The patient is a male aged 18–29, this is a close-up image, the affected area is the leg: 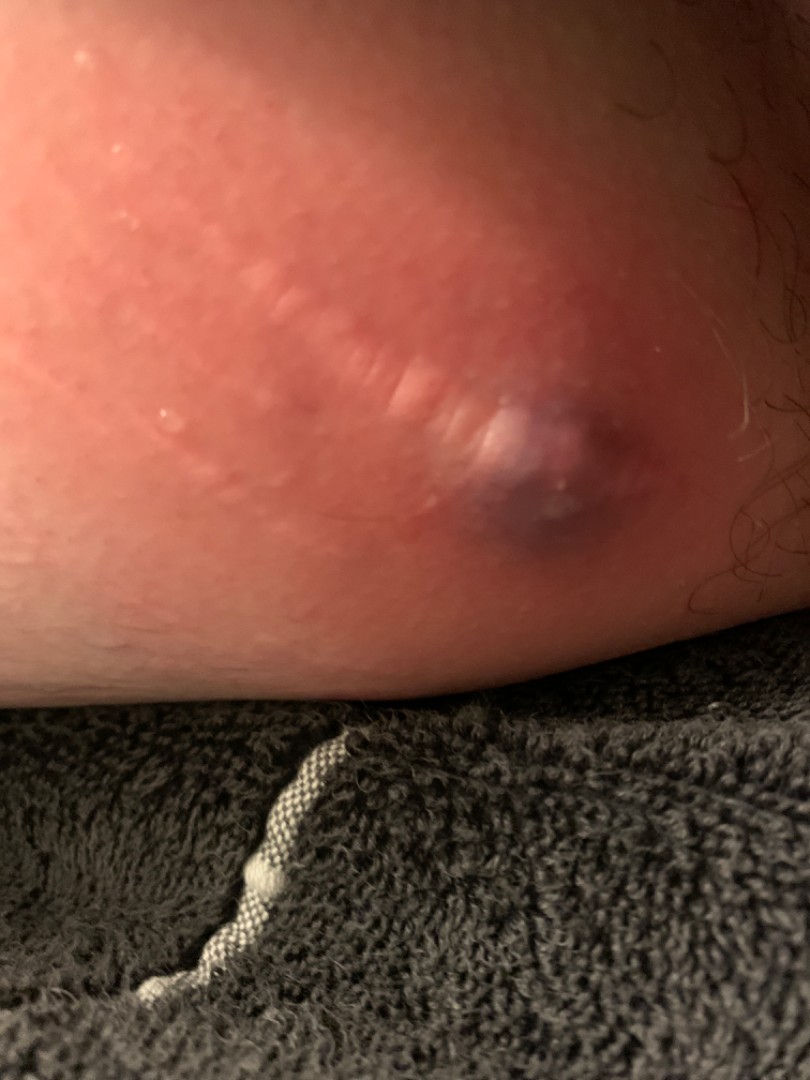Patient information: The condition has been present for less than one week. The patient reported no systemic symptoms. The patient considered this a rash. Review: On remote review of the image: favoring Abscess; also consider Cyst.